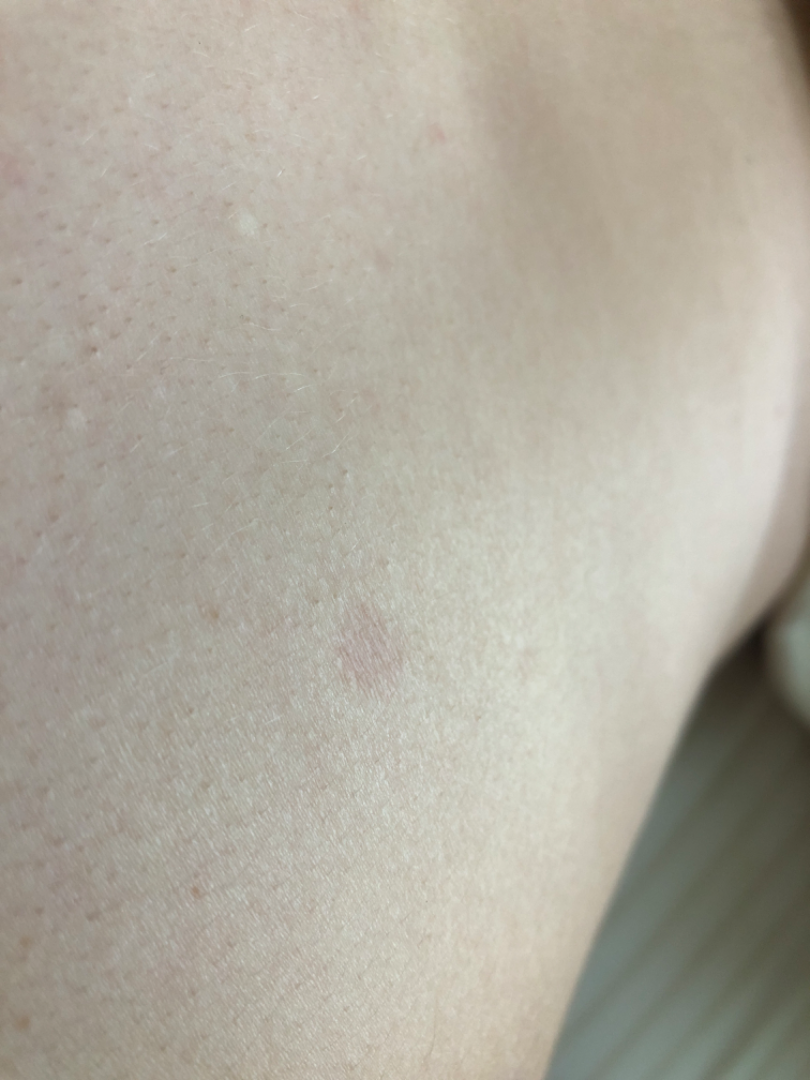Q: What was the assessment?
A: indeterminate
Q: What is the affected area?
A: front of the torso and back of the torso
Q: Fitzpatrick or Monk tone?
A: lay graders estimated Monk skin tone scale 2 or 3
Q: Constitutional symptoms?
A: fatigue
Q: What is the lesion texture?
A: flat
Q: Age and sex?
A: male, age 18–29
Q: Image view?
A: at an angle
Q: Patient's own categorization?
A: a rash
Q: When did this start?
A: one to three months